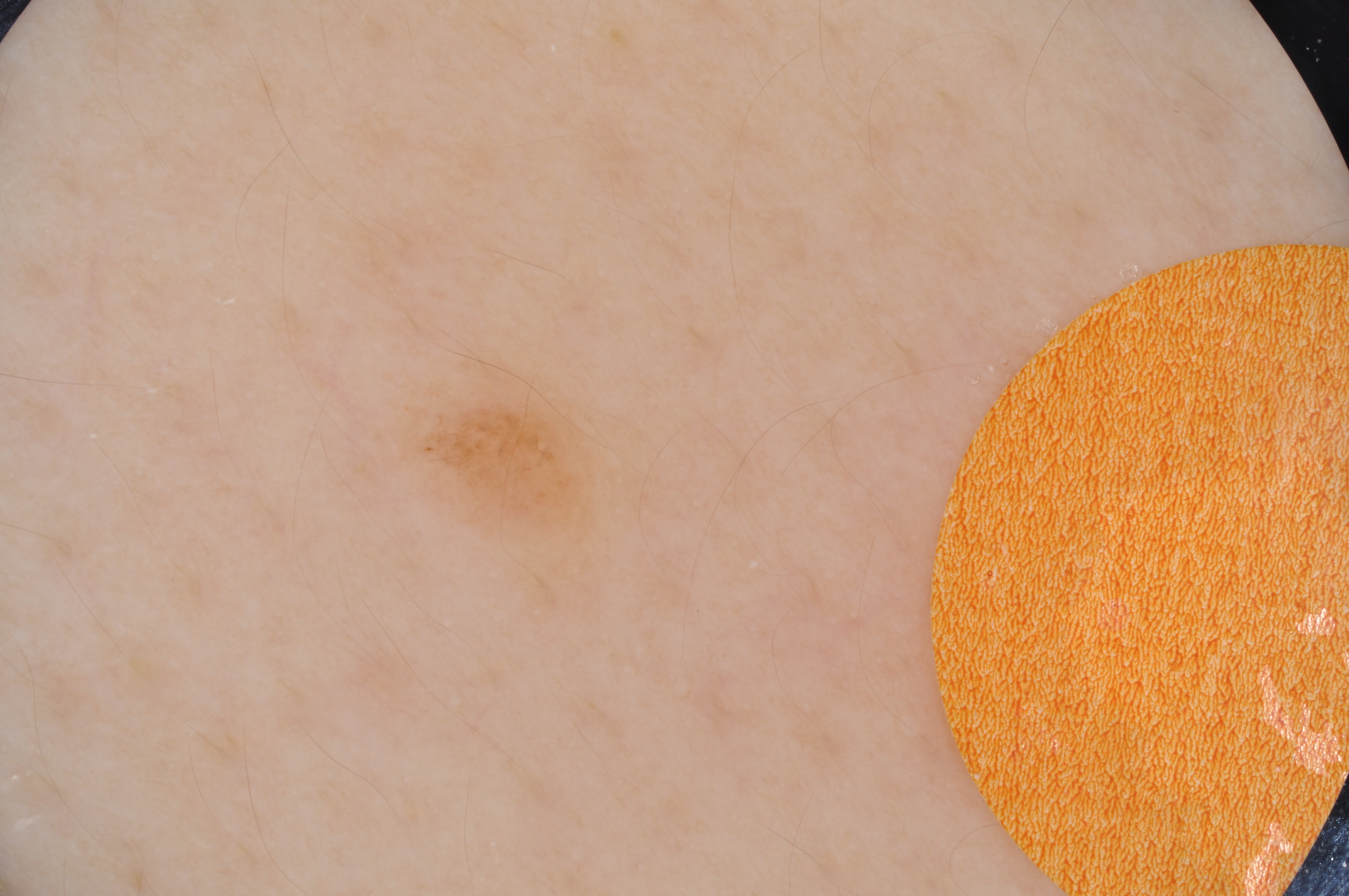image type = dermoscopy of a skin lesion | lesion location = 381 346 653 580 | impression = a melanocytic nevus, a benign lesion.